A dermoscopy image of a skin lesion · a male subject age 89 · imaged for a research study, with no referral diagnosis recorded:
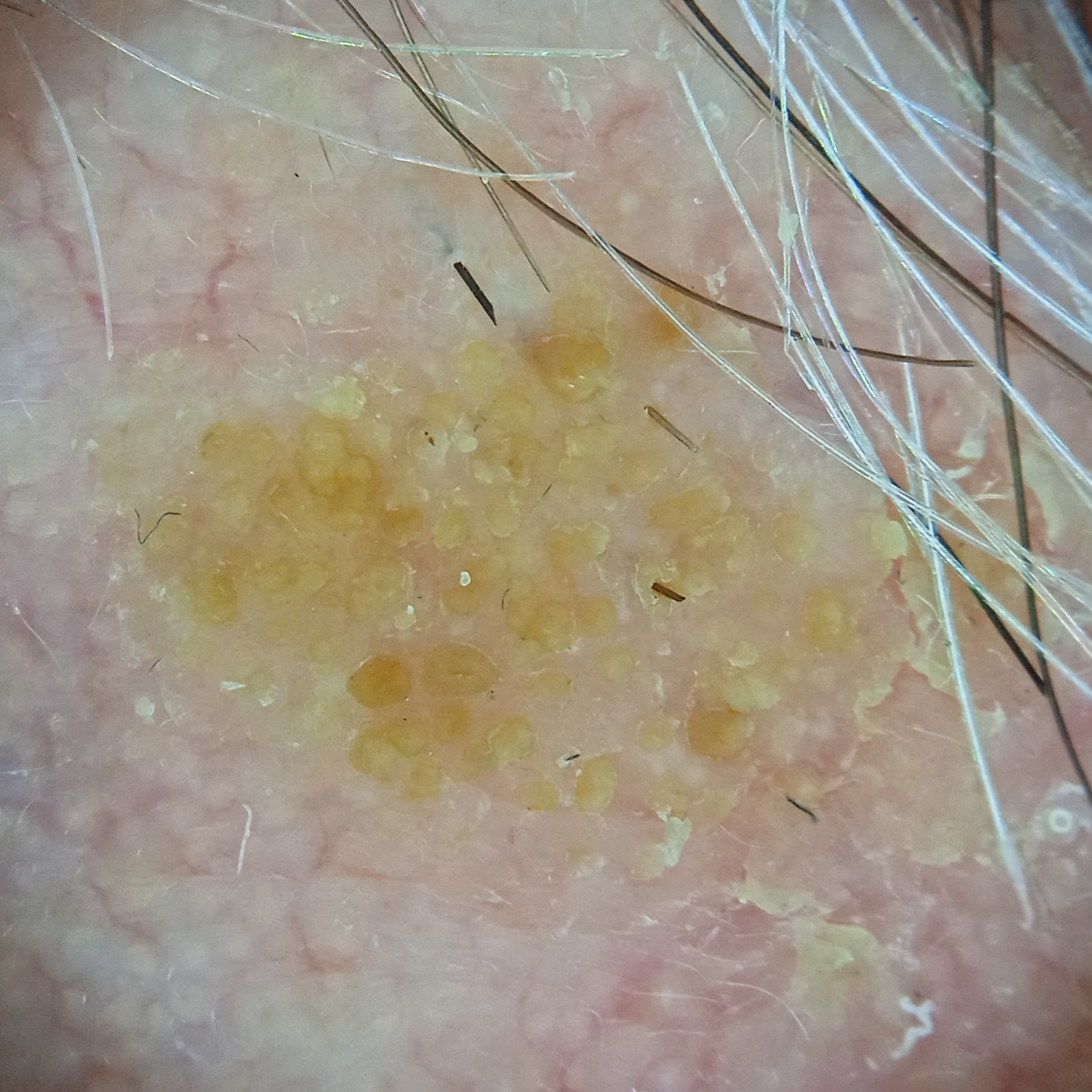anatomic site: the face | diagnostic label: seborrheic keratosis (dermatologist consensus).